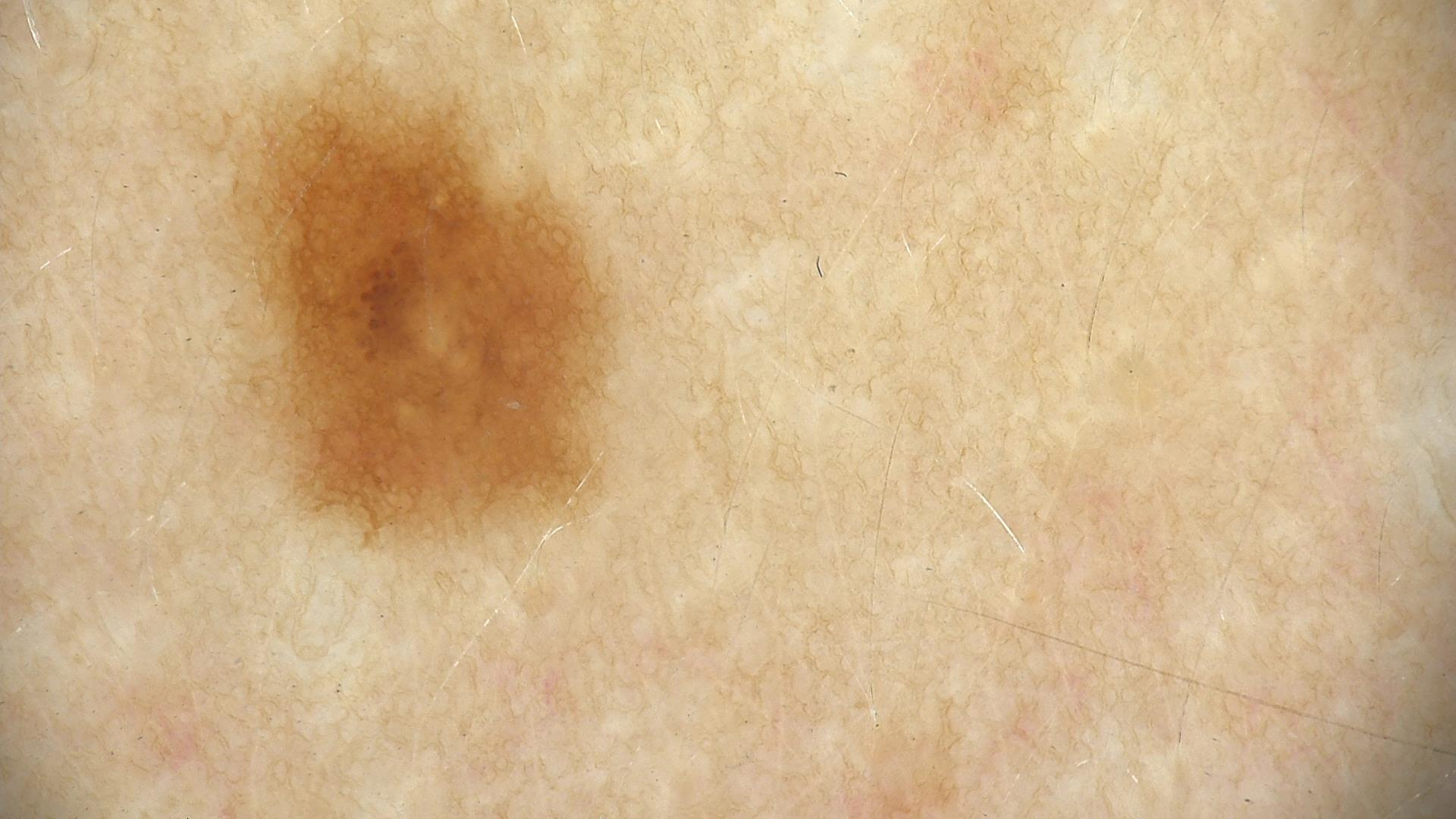Q: What is the imaging modality?
A: dermatoscopy
Q: What is the diagnosis?
A: dysplastic junctional nevus (expert consensus)